A dermoscopic close-up of a skin lesion.
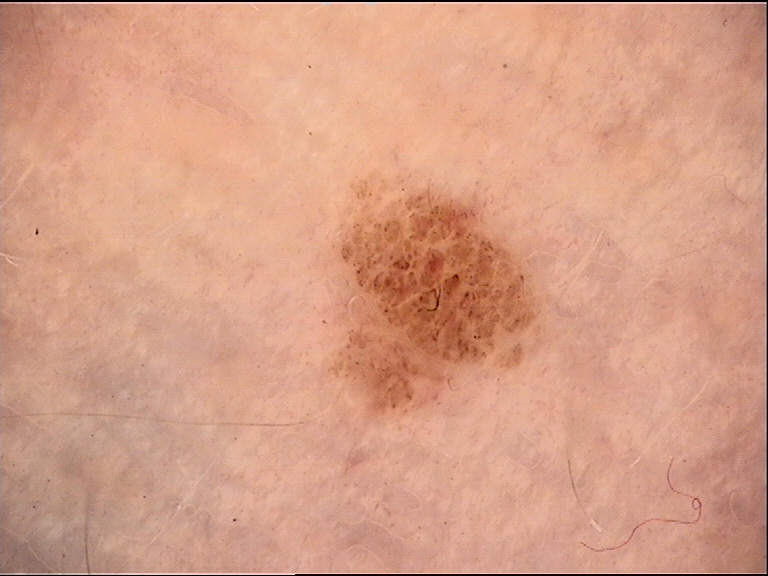The morphology is that of a banal lesion.
Diagnosed as a compound nevus.